Fitzpatrick phototype V; an image taken at a distance — 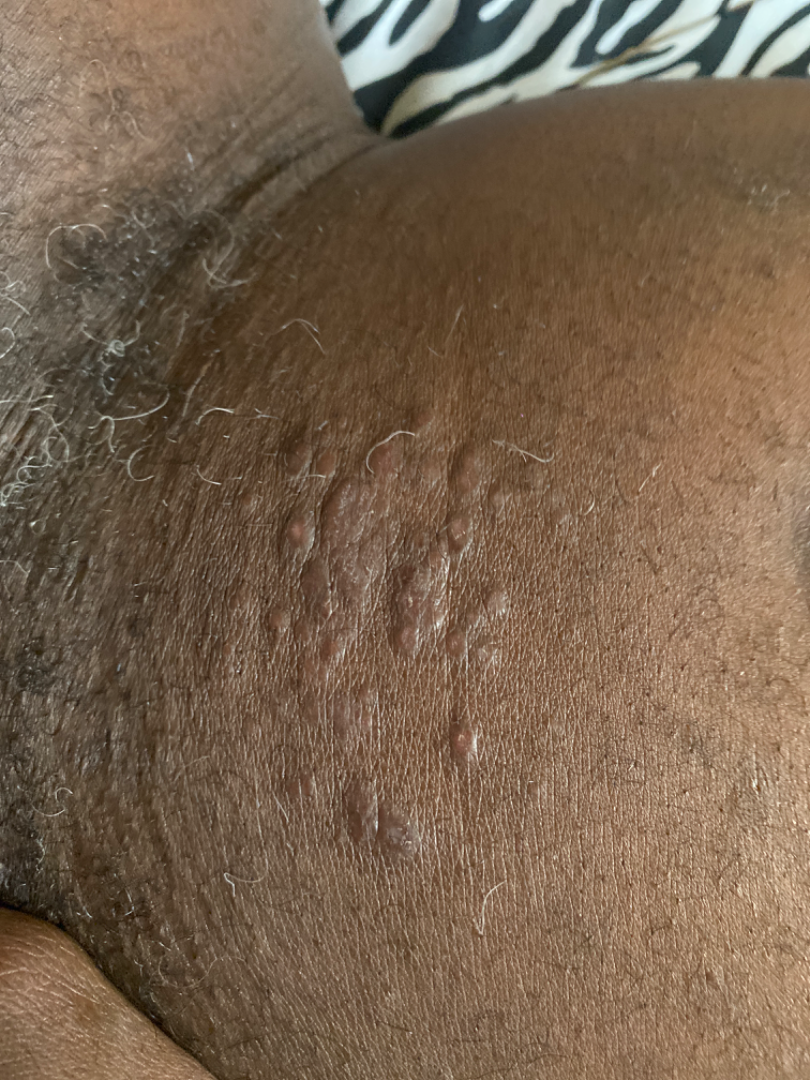dermatologist impression = the favored diagnosis is Allergic Contact Dermatitis; with consideration of Eczema; the differential also includes Verruca vulgaris